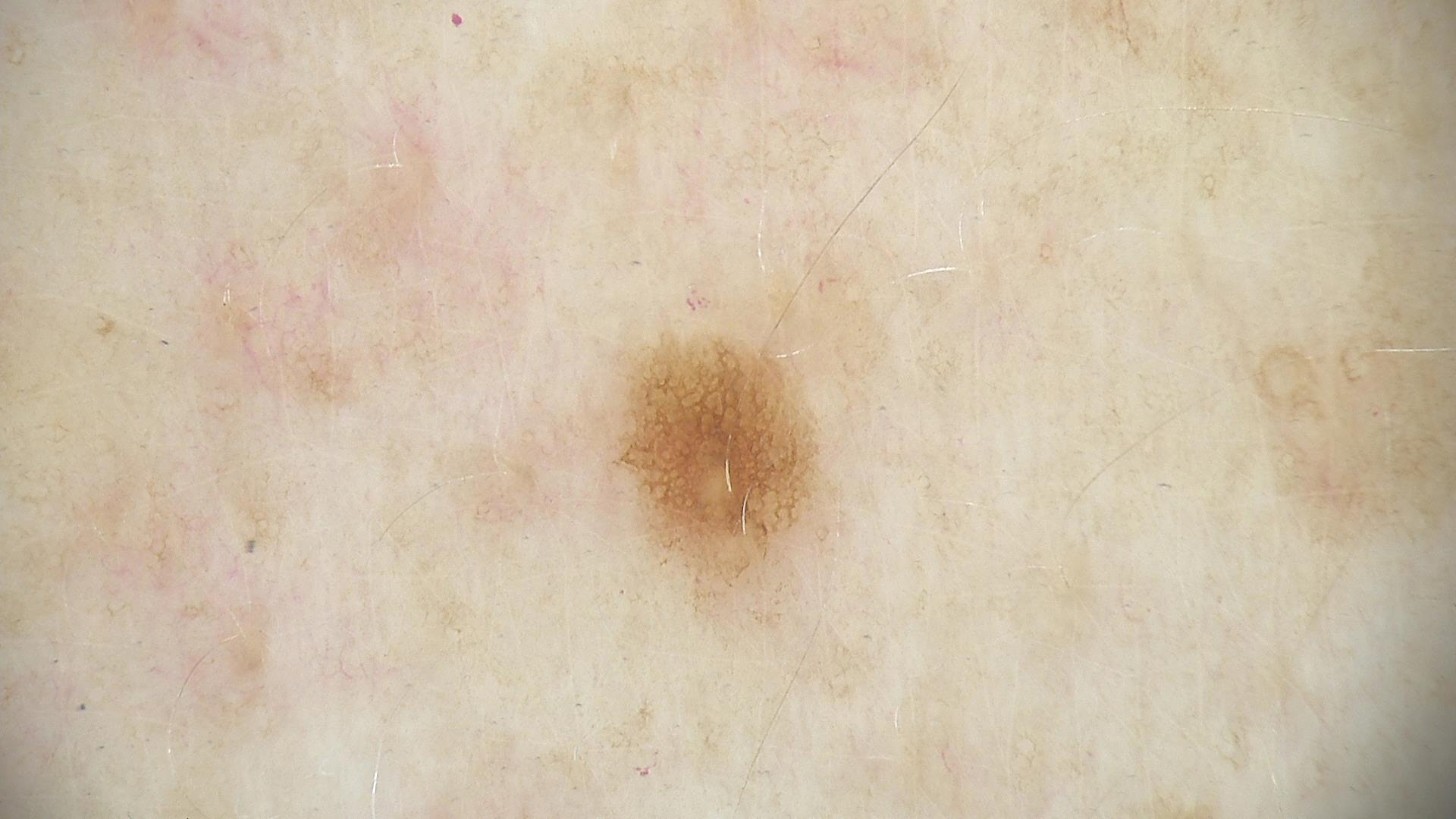Conclusion:
Classified as a dysplastic junctional nevus.